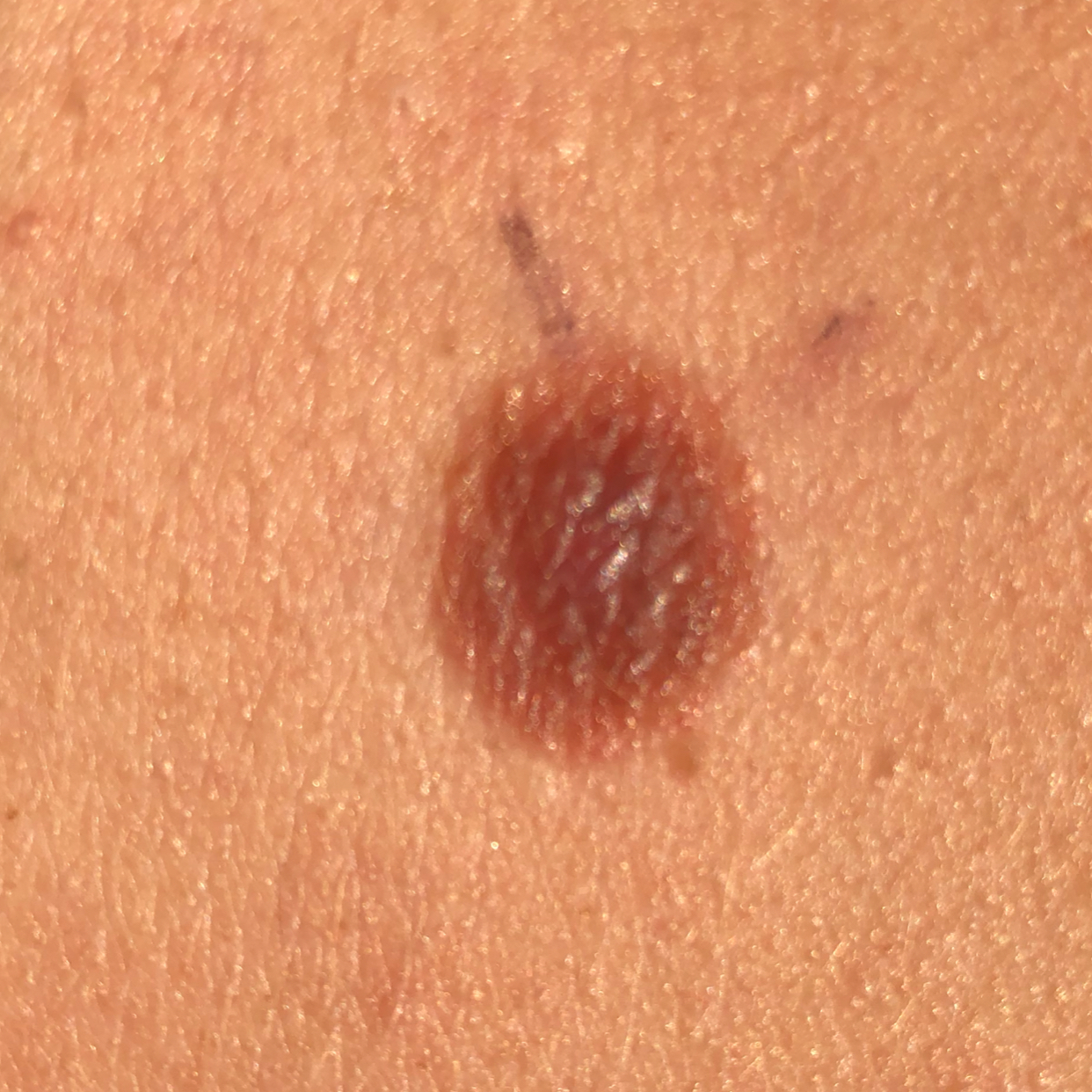Summary:
The lesion involves the back. The patient reports that the lesion is elevated and has grown.
Conclusion:
Expert review favored a nevus.